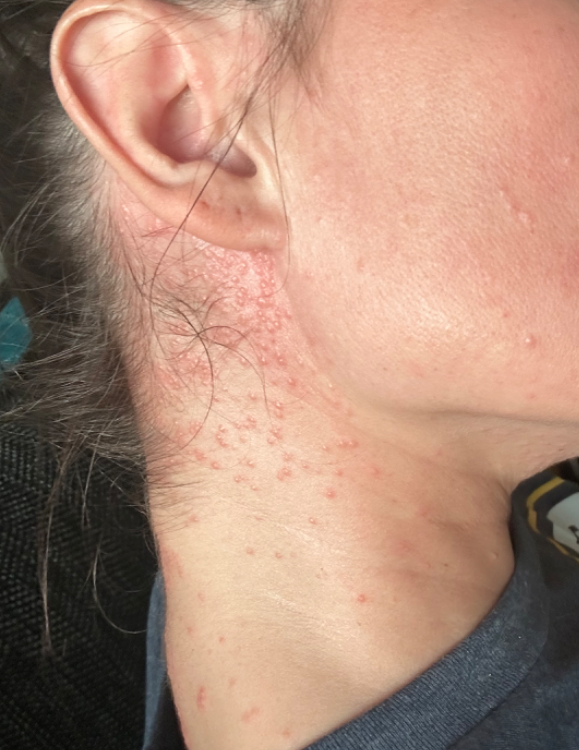Review:
No differential diagnosis could be assigned on photographic review.
Patient information:
The lesion involves the head or neck. The photograph was taken at an angle.